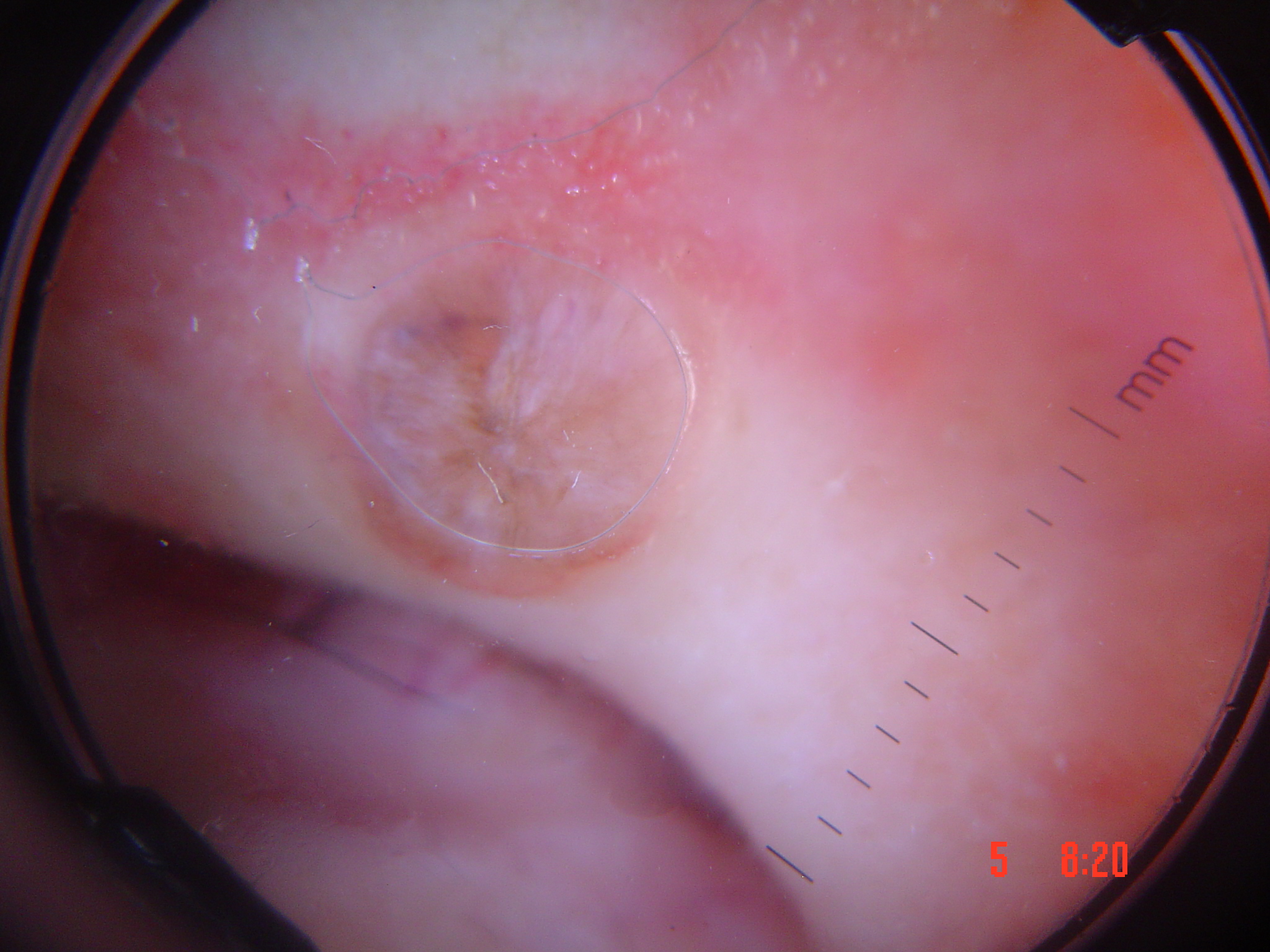modality=dermatoscopy; class=basal cell carcinoma (biopsy-proven).